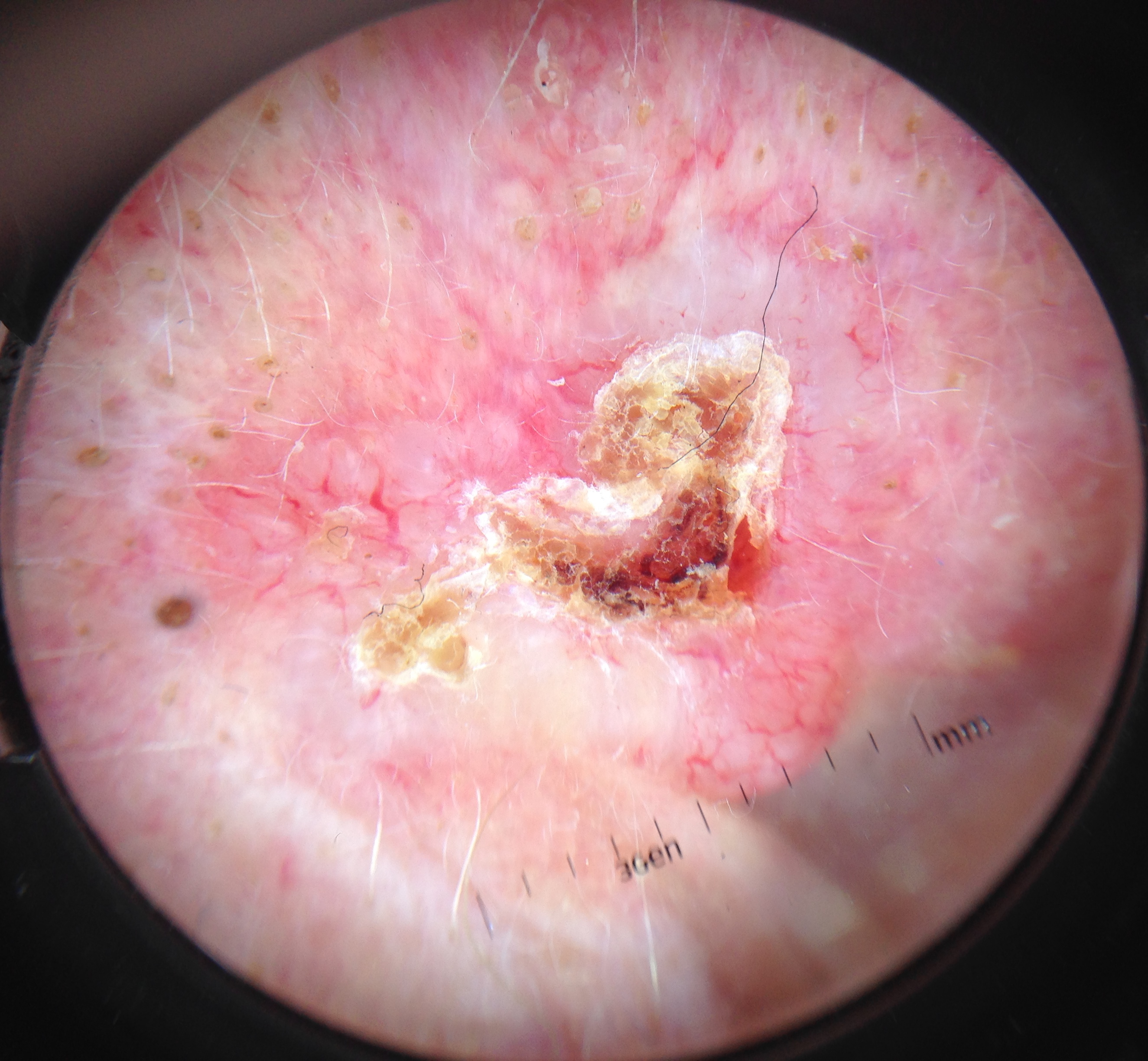Conclusion: Confirmed on histopathology as a keratinocytic lesion — a basal cell carcinoma.